This is a close-up image. Located on the top or side of the foot.
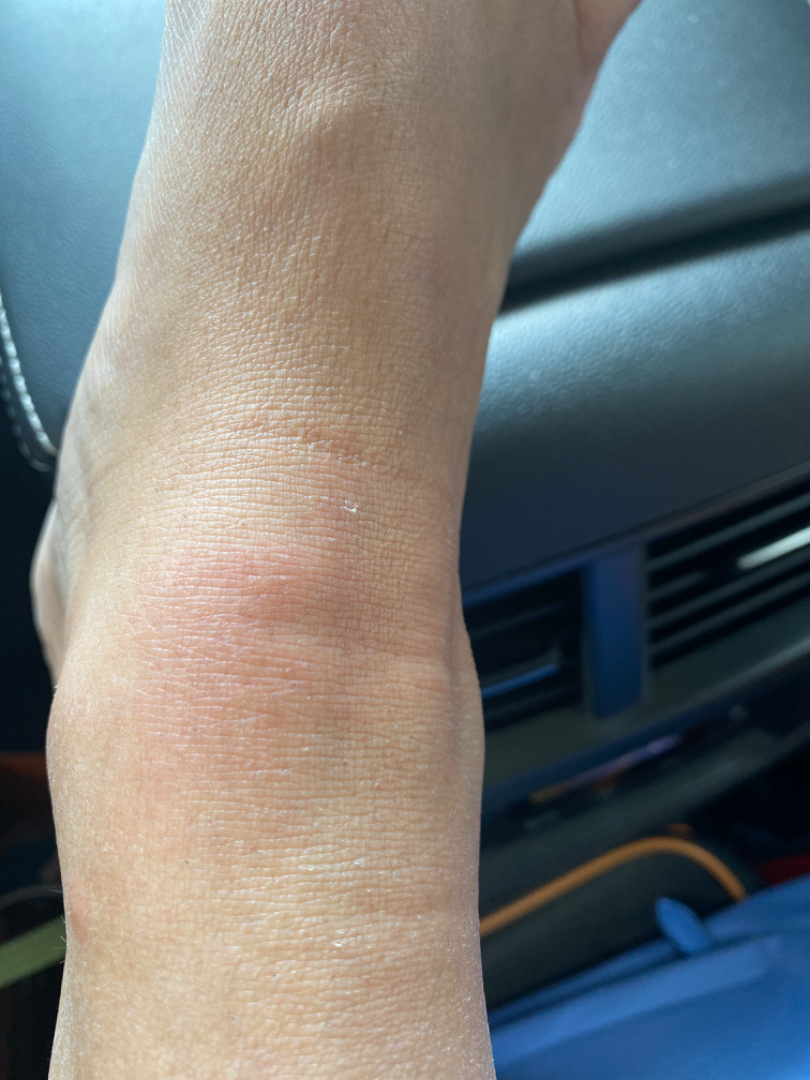assessment: no clear pathology